A female patient, aged around 70. A dermatoscopic image of a skin lesion.
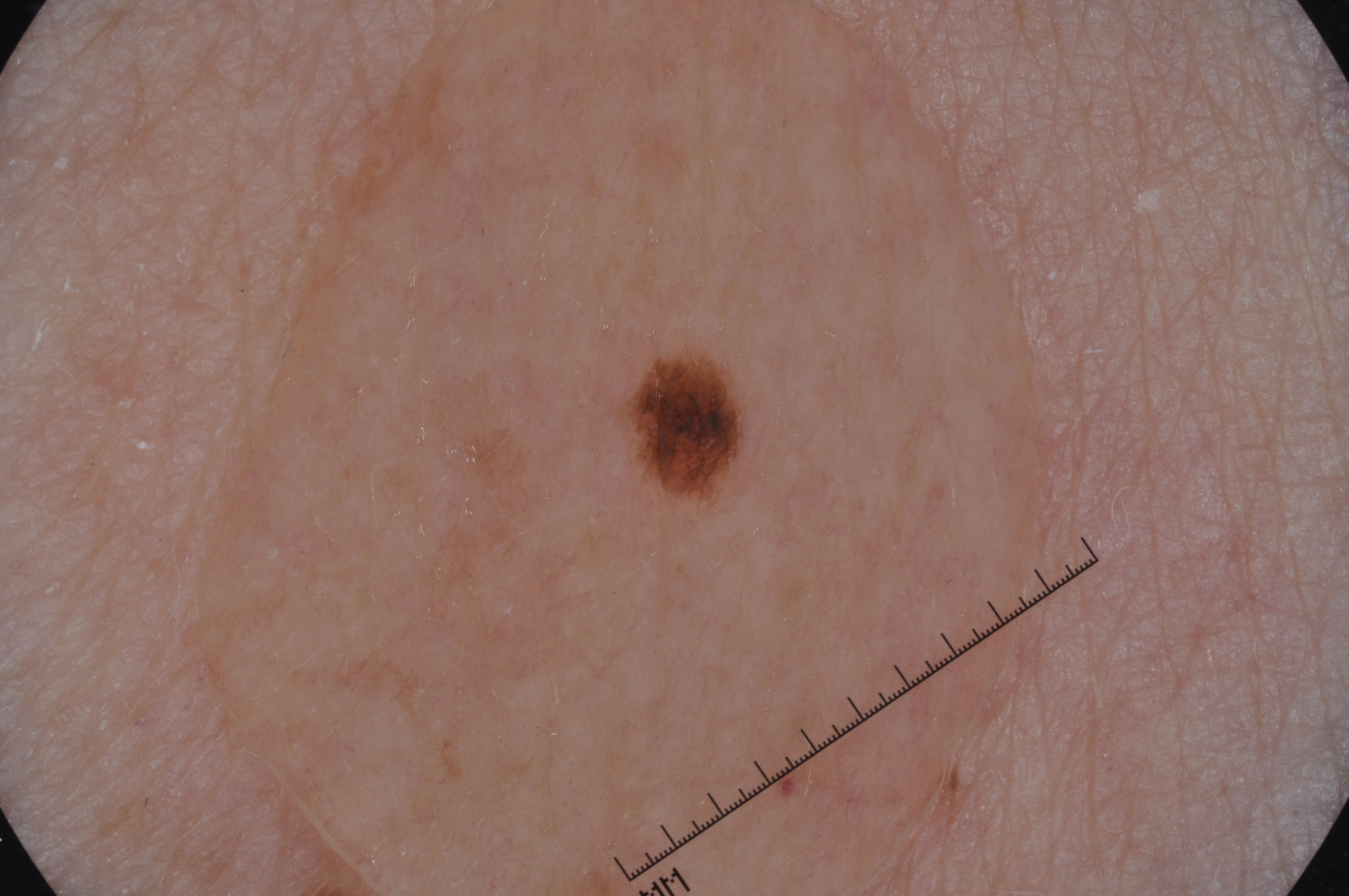The dermoscopic pattern shows pigment network.
In (x1, y1, x2, y2) order, the lesion occupies the region bbox(606, 345, 750, 503).
The diagnostic assessment was a melanocytic nevus, a benign lesion.